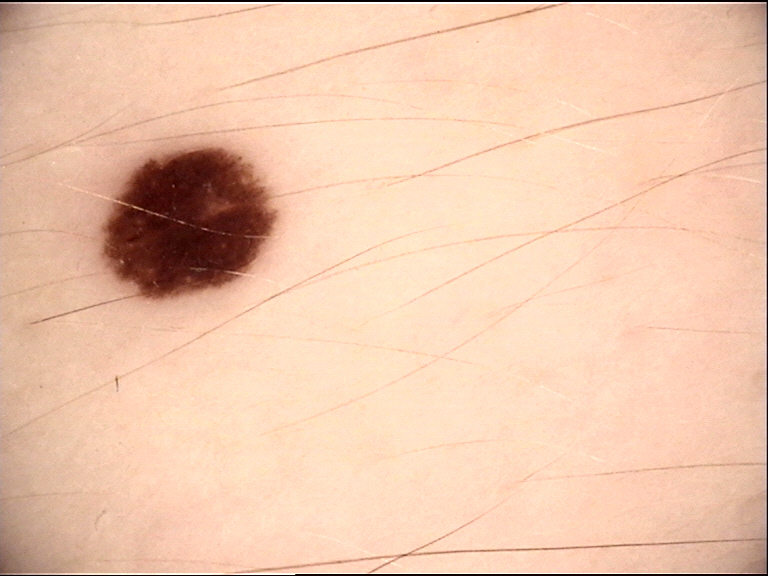A skin lesion imaged with a dermatoscope. This is a banal lesion. Classified as a junctional nevus.